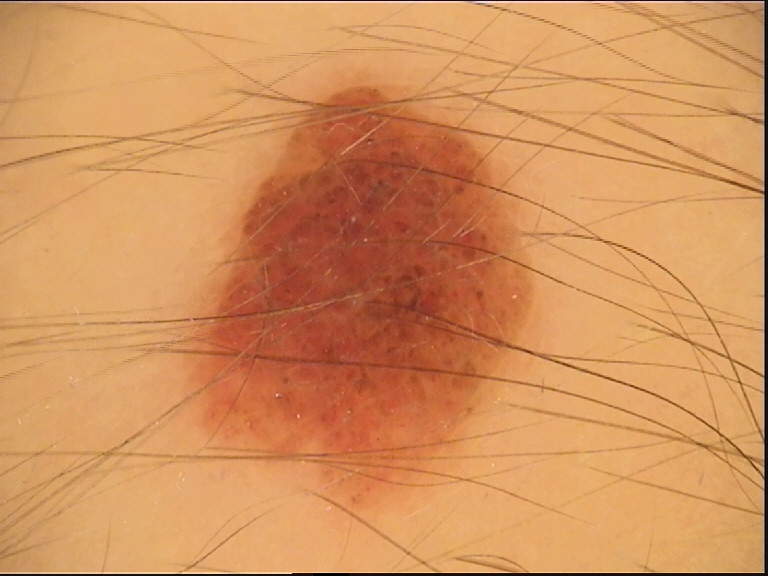<dermoscopy>
<image>dermatoscopy</image>
<diagnosis>
<name>compound nevus</name>
<code>cb</code>
<malignancy>benign</malignancy>
<super_class>melanocytic</super_class>
<confirmation>expert consensus</confirmation>
</diagnosis>
</dermoscopy>